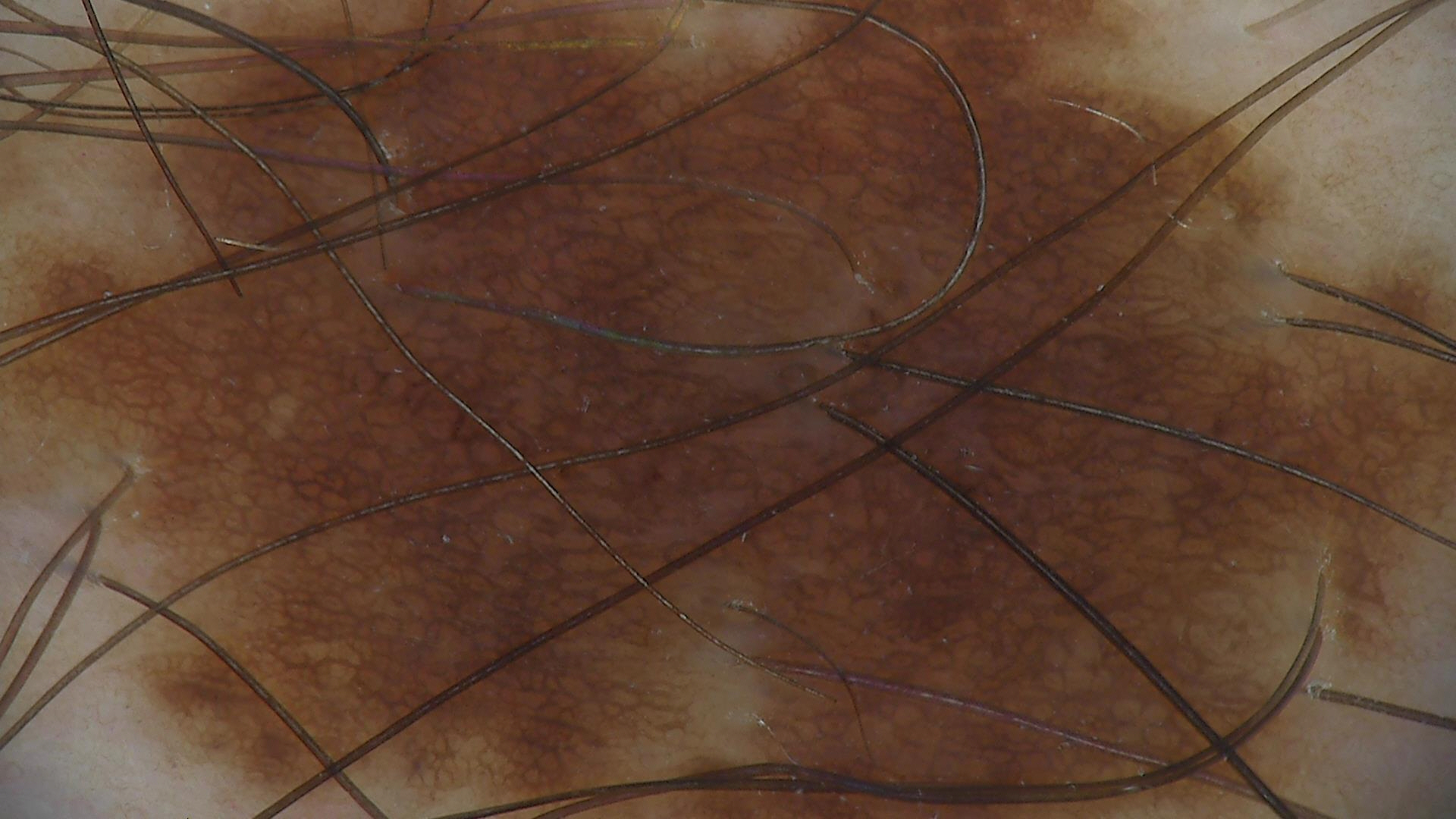The diagnostic label was a dysplastic junctional nevus.